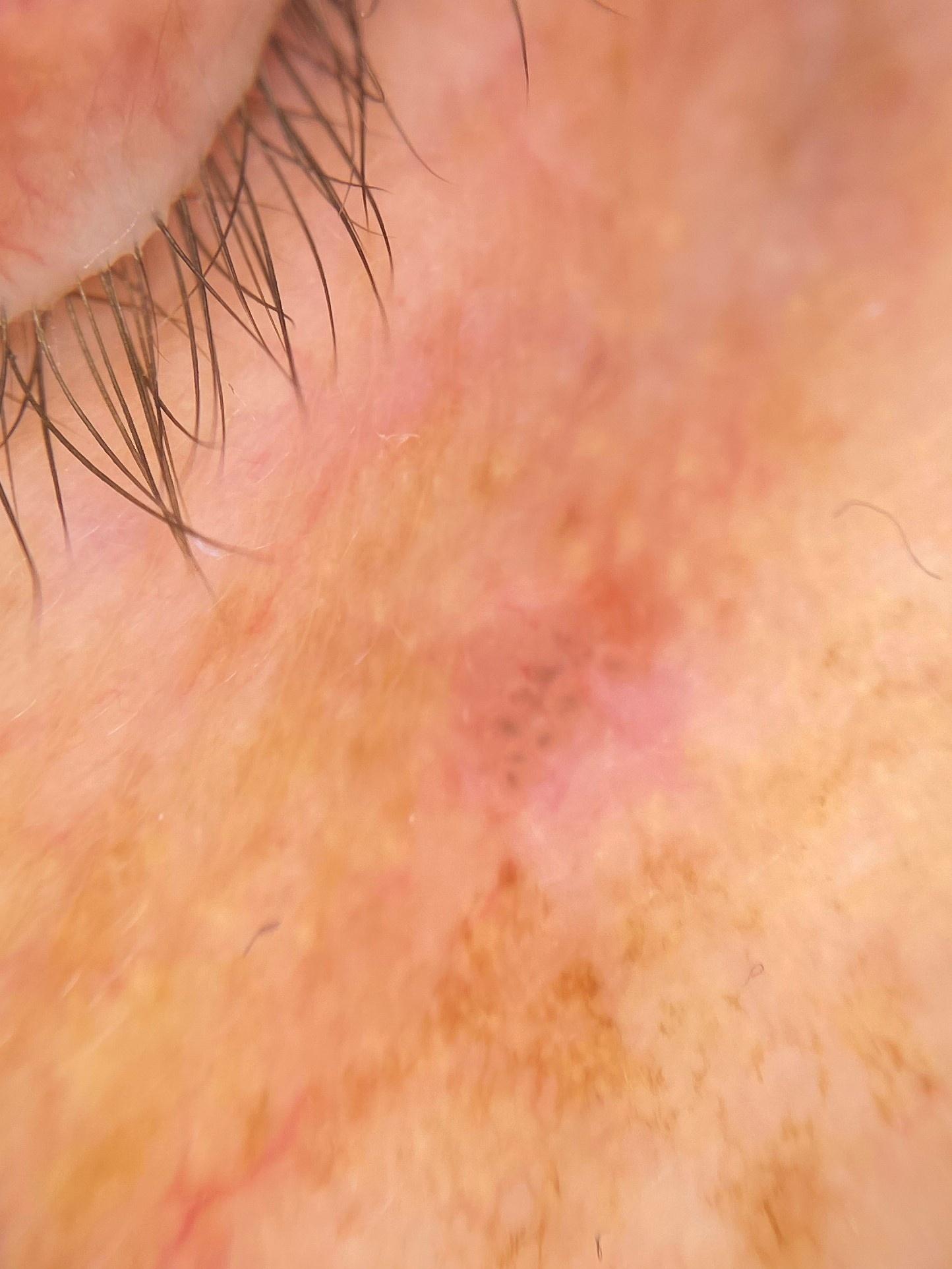FST — II
patient — female, about 60 years old
anatomic site — the head or neck
diagnosis — Basal cell carcinoma (biopsy-proven)